A dermoscopic photograph of a skin lesion.
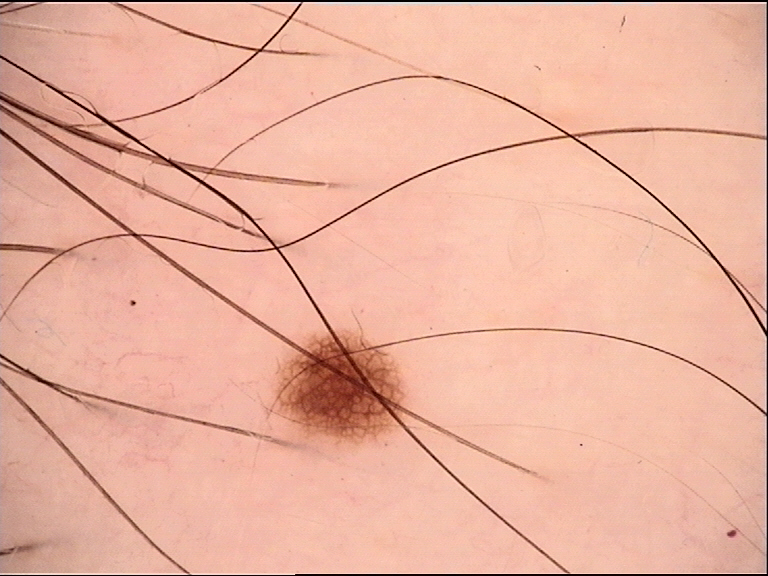The diagnostic label was a dysplastic junctional nevus.